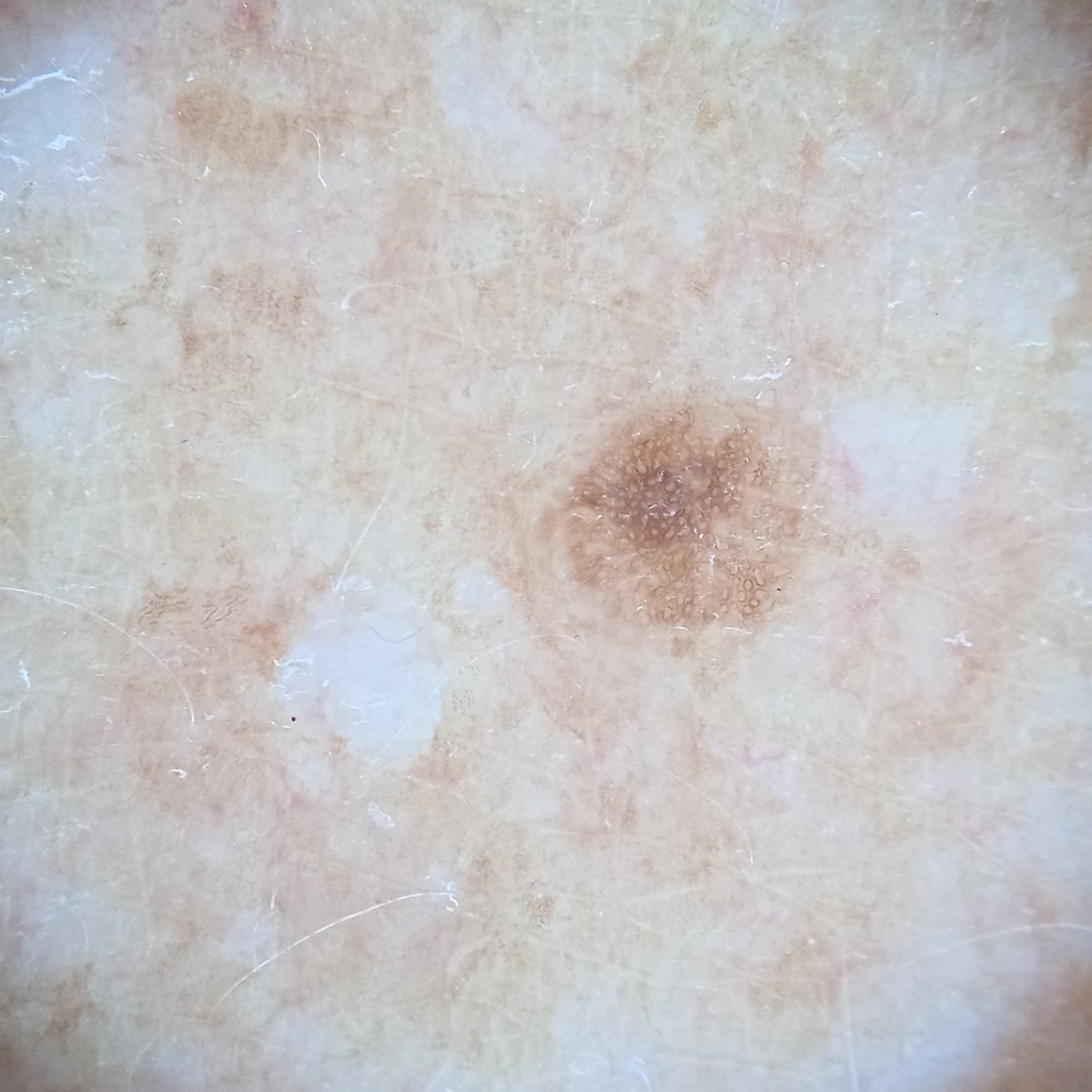| feature | finding |
|---|---|
| assessment | melanocytic nevus (dermatologist consensus) |